A dermoscopic close-up of a skin lesion.
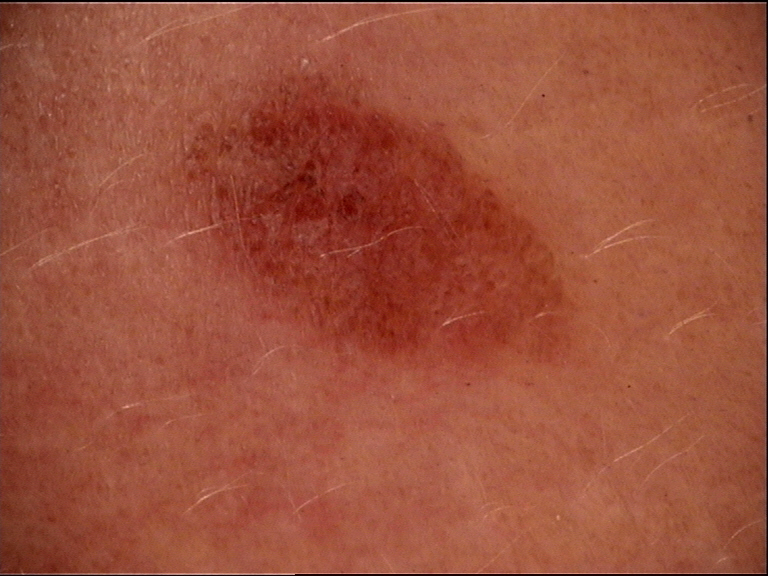The architecture is that of a banal lesion. Classified as a compound nevus.